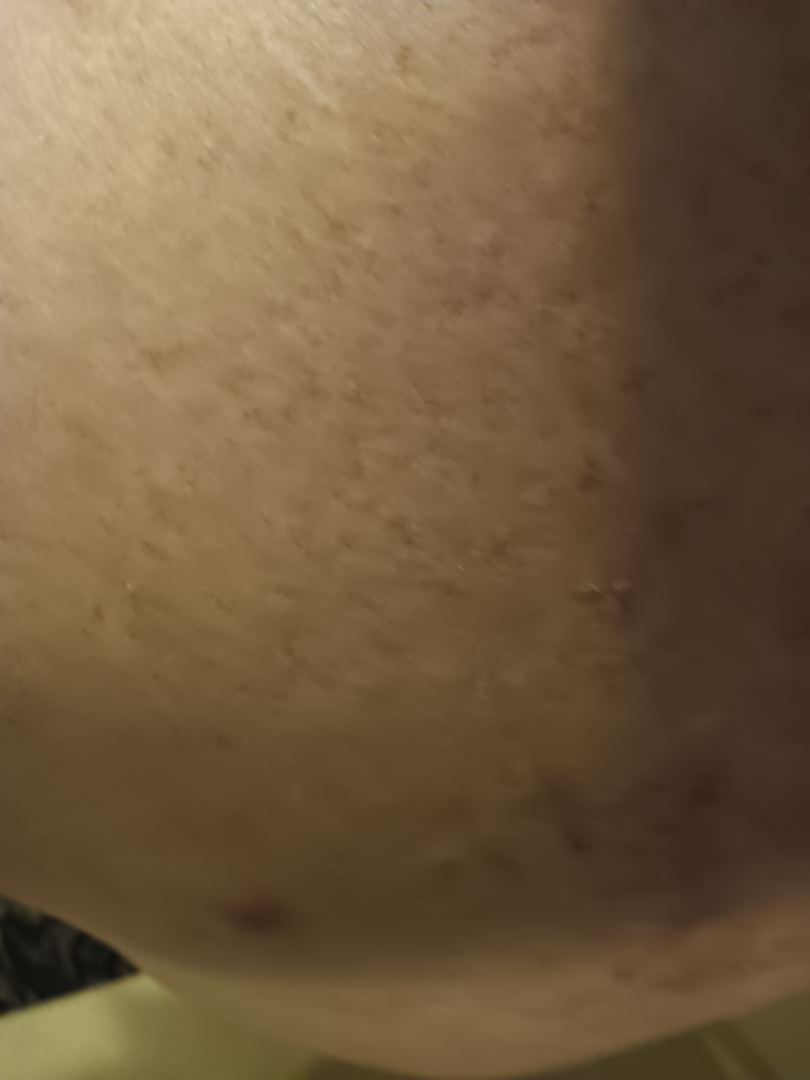Patient information: The lesion involves the back of the torso. The photograph is a close-up of the affected area. The subject is 50–59, male.